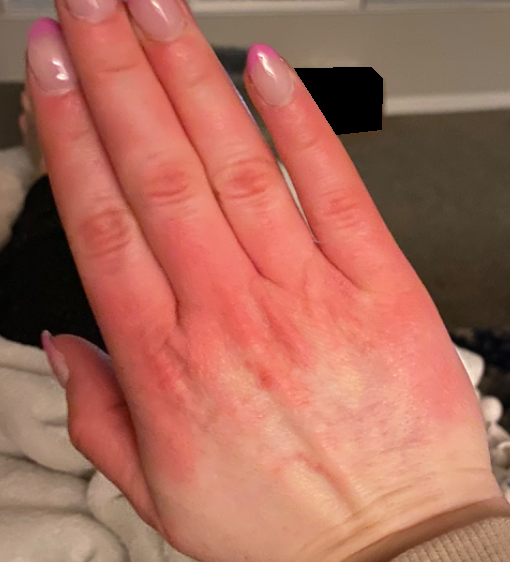Clinical context: The patient is 18–29, female. A close-up photograph. Assessment: On dermatologist assessment of the image: the favored diagnosis is Irritant Contact Dermatitis; also consider Acral erythema; an alternative is Allergic Contact Dermatitis.